Female contributor, age 50–59 · close-up view · located on the head or neck, back of the torso and front of the torso:
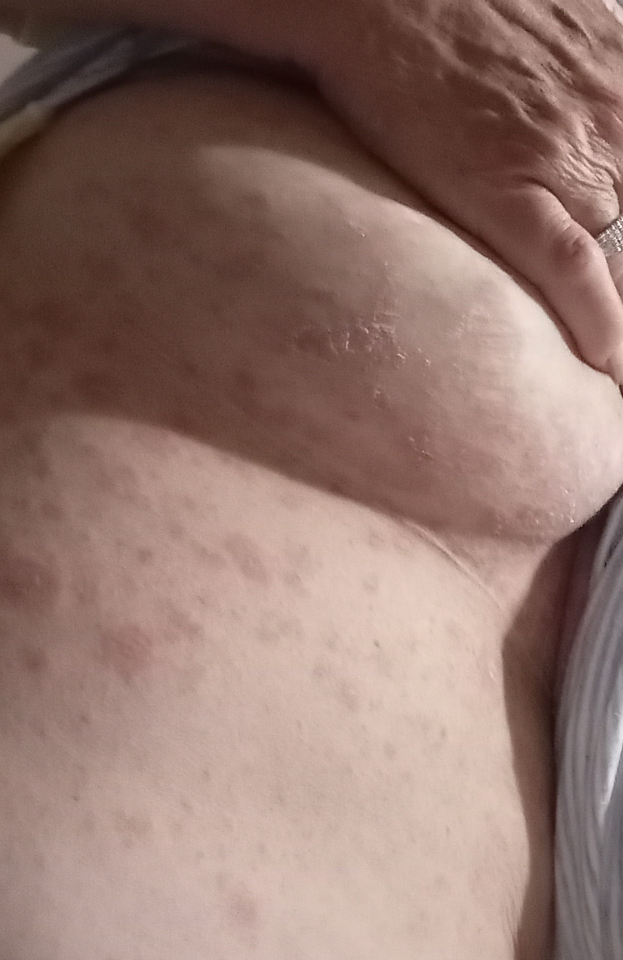On dermatologist assessment of the image: the impression is Psoriasis.